A dermoscopy image of a single skin lesion: 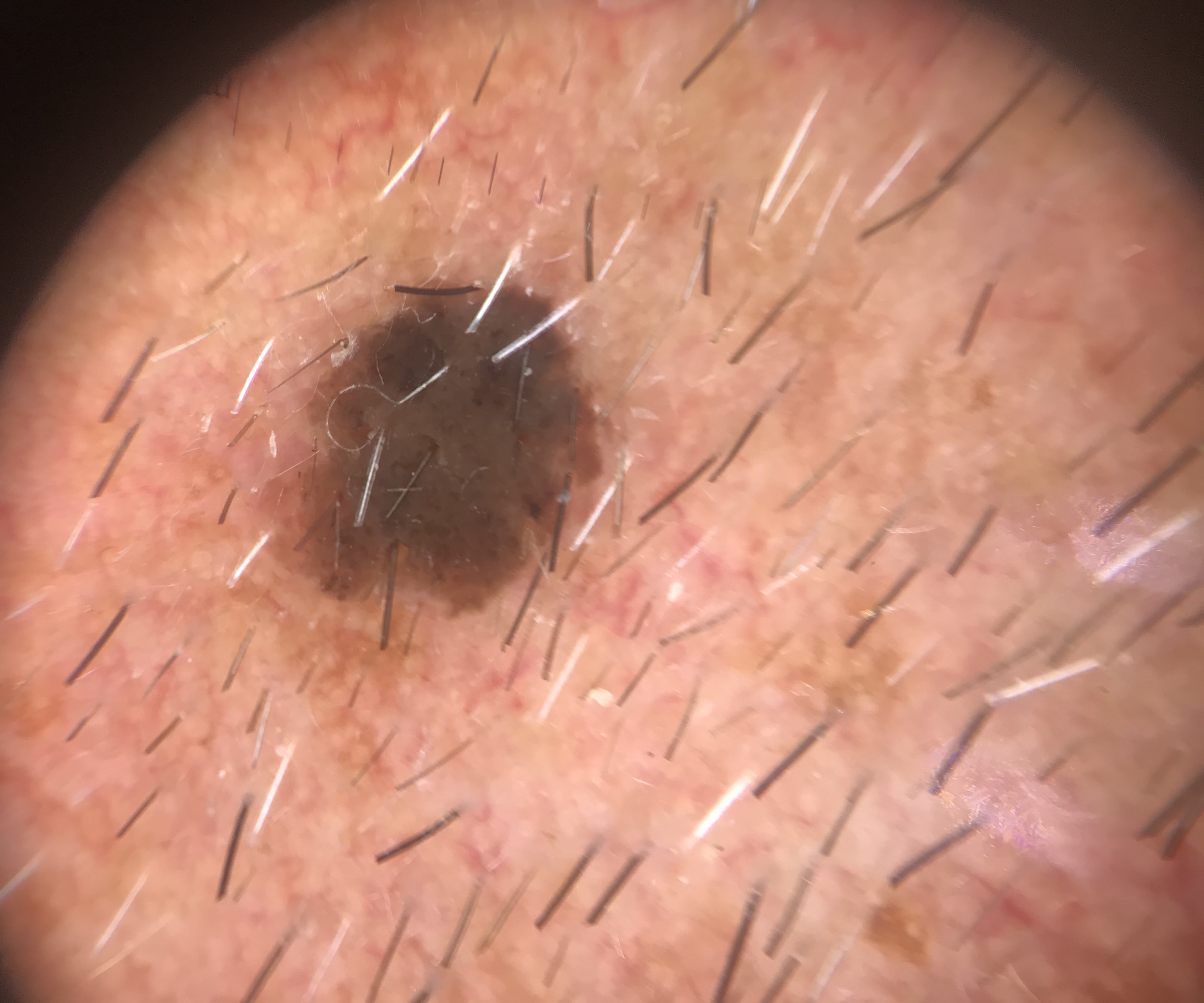Q: How is the lesion classified?
A: keratinocytic
Q: What was the diagnostic impression?
A: seborrheic keratosis (expert consensus)